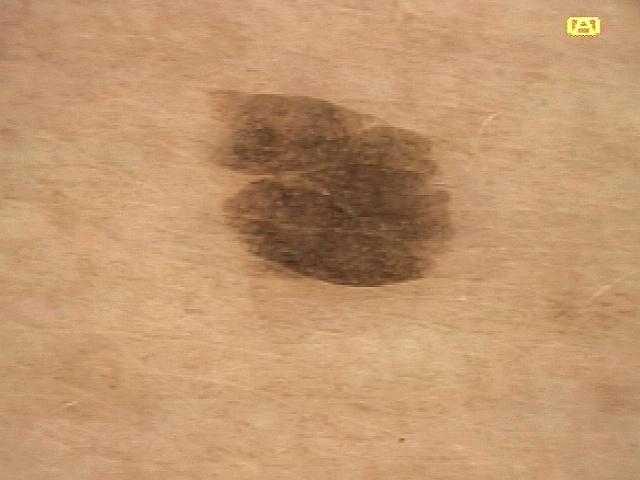Summary:
Recorded as Fitzpatrick skin type II. A dermoscopic image of a skin lesion. The lesion is on the trunk.
Impression:
Consistent with an epidermal lesion — a seborrheic keratosis.